The photo was captured at an angle · the lesion involves the leg — 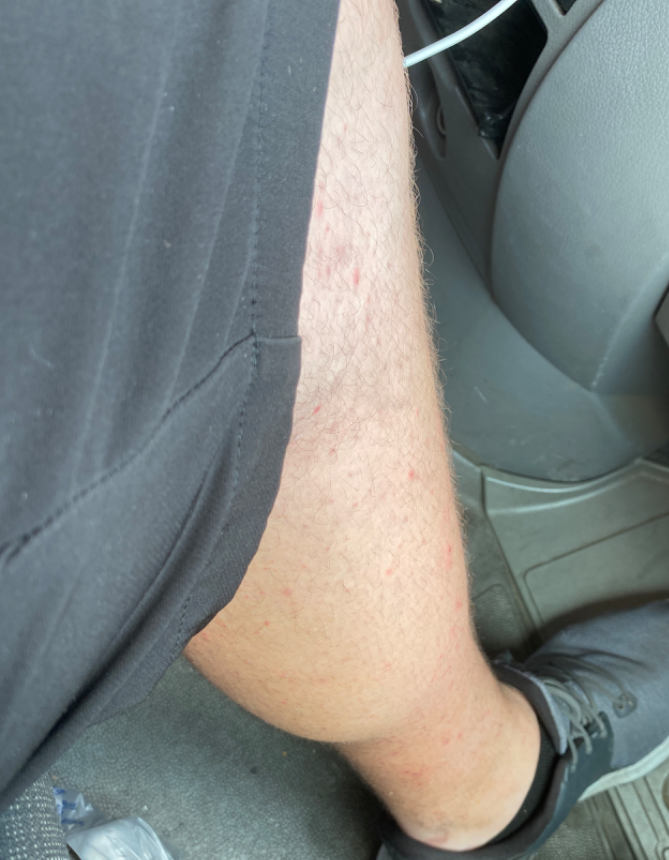The reviewer was unable to grade this case for skin condition. The contributor notes burning, itching and bothersome appearance. Skin tone: Fitzpatrick II. Reported duration is less than one week. The patient considered this acne. Texture is reported as raised or bumpy.